The photo was captured at a distance. Female patient, age 18–29. The leg, back of the torso and front of the torso are involved — 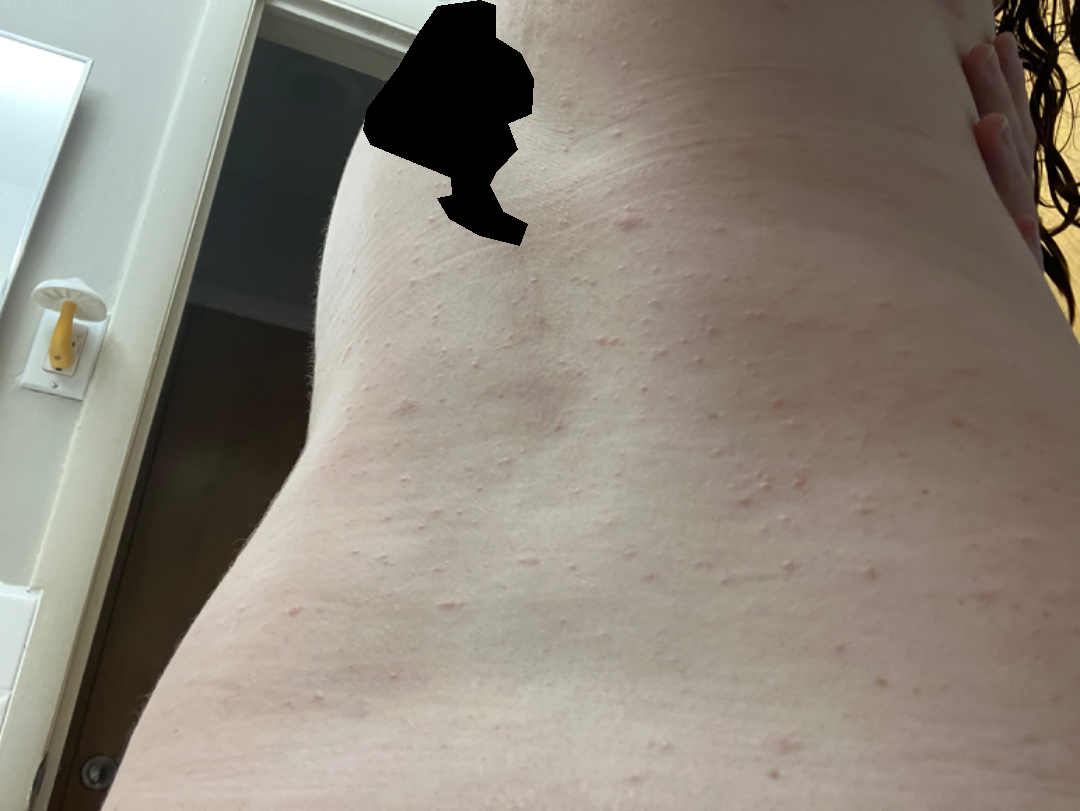differential diagnosis — the impression on review was Urticaria.